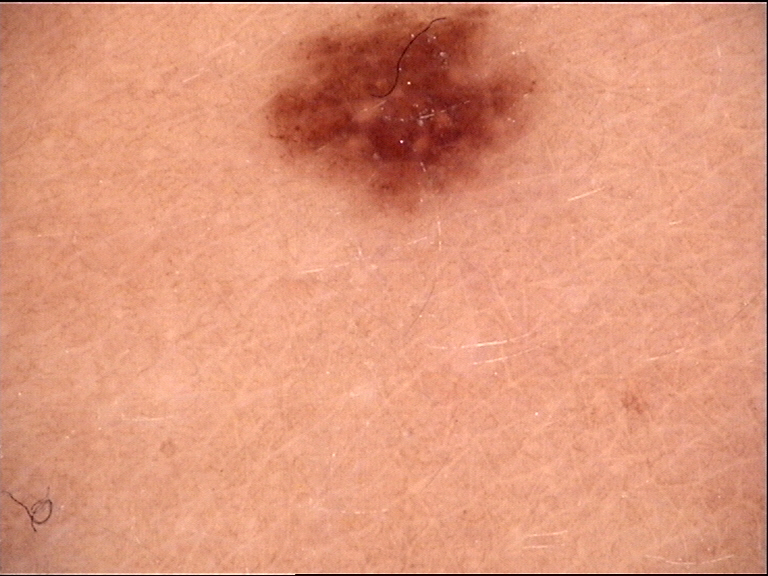The diagnosis was a dysplastic junctional nevus.